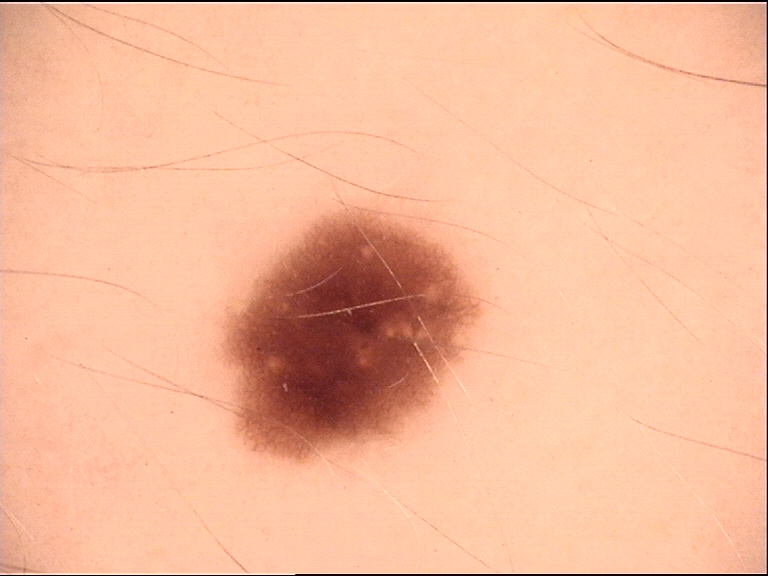Impression: Consistent with a dysplastic junctional nevus.